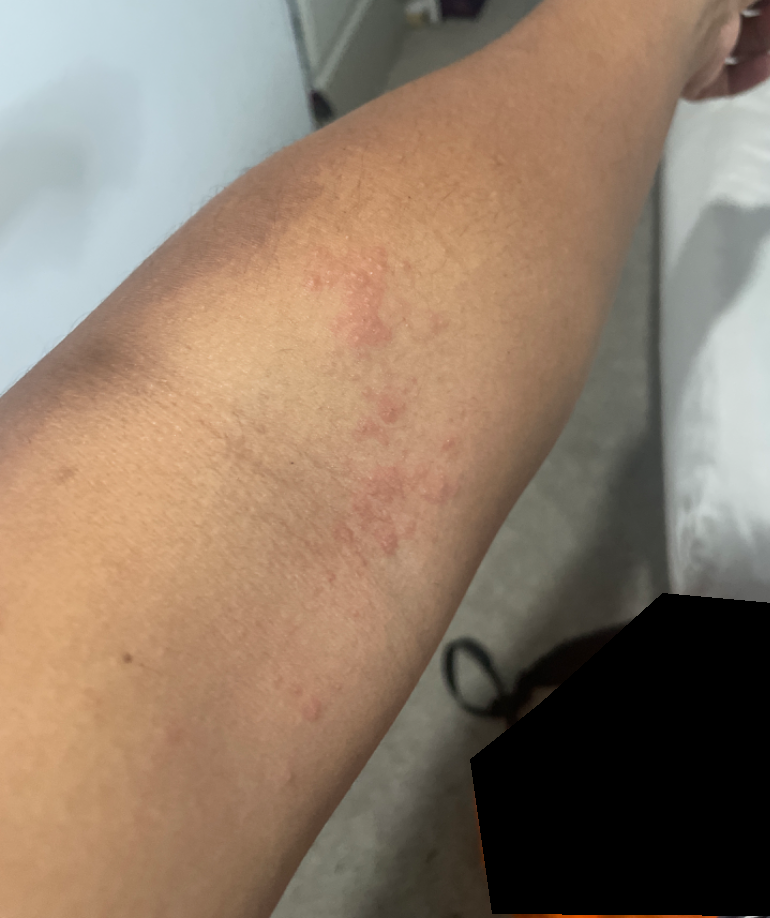- patient describes the issue as · acne
- shot type · at an angle
- contributor · male, age 18–29
- symptoms · itching and bothersome appearance
- texture · raised or bumpy
- location · arm and back of the hand
- differential diagnosis · reviewed remotely by three dermatologists: the primary impression is Eczema; possibly Allergic Contact Dermatitis